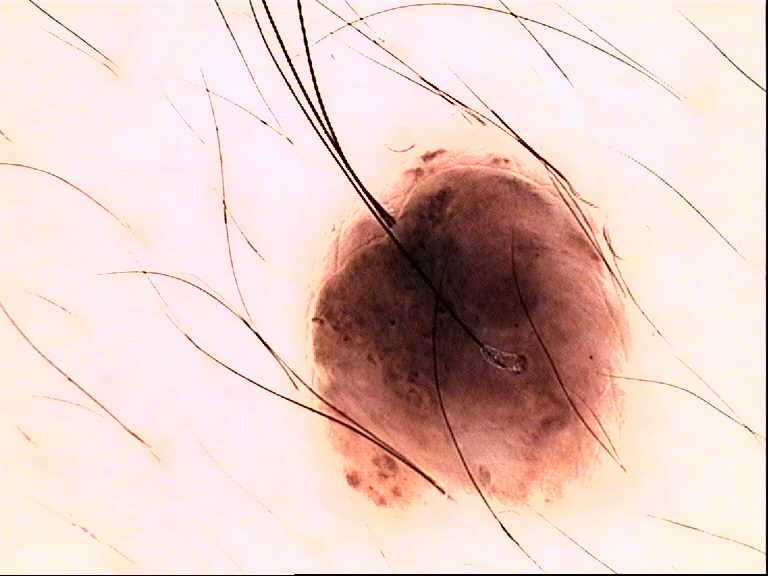Conclusion:
Classified as a banal lesion — a congenital compound nevus.